The photograph is a close-up of the affected area — 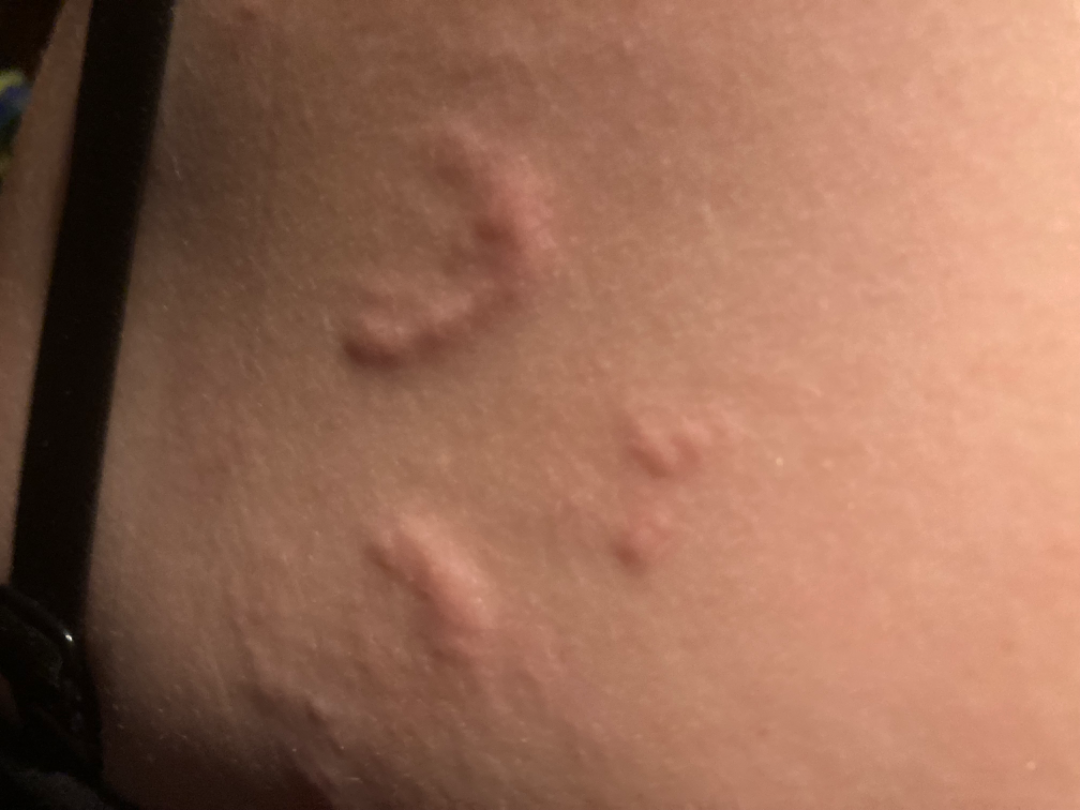assessment = not assessable.